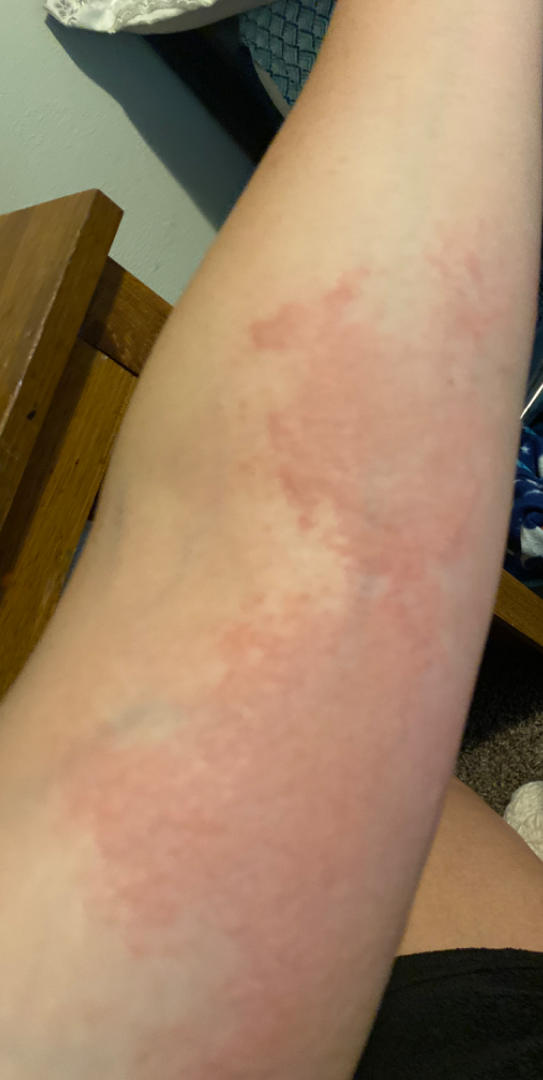{"differential": {"leading": ["Eczema"], "considered": ["Urticaria", "Psoriasis"]}}